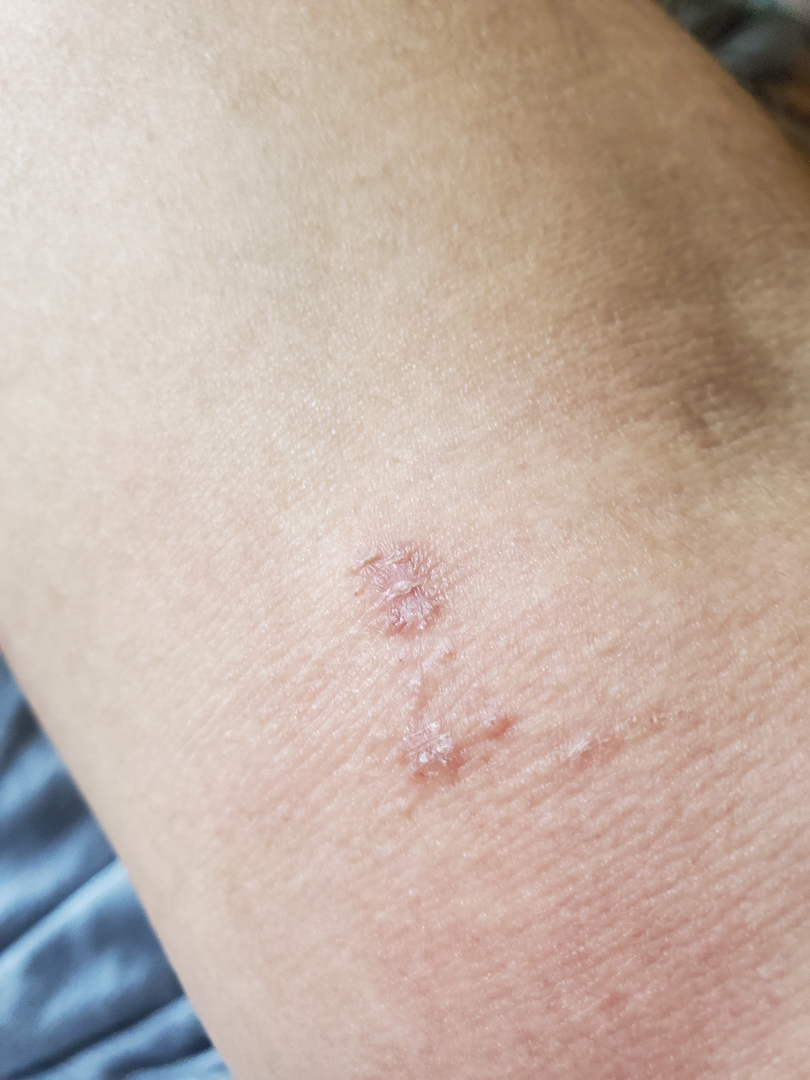Three independent reviewers: the differential includes Psoriasis, Lichen Simplex Chronicus and Eczema, with no clear leading consideration.